A close-up photograph.
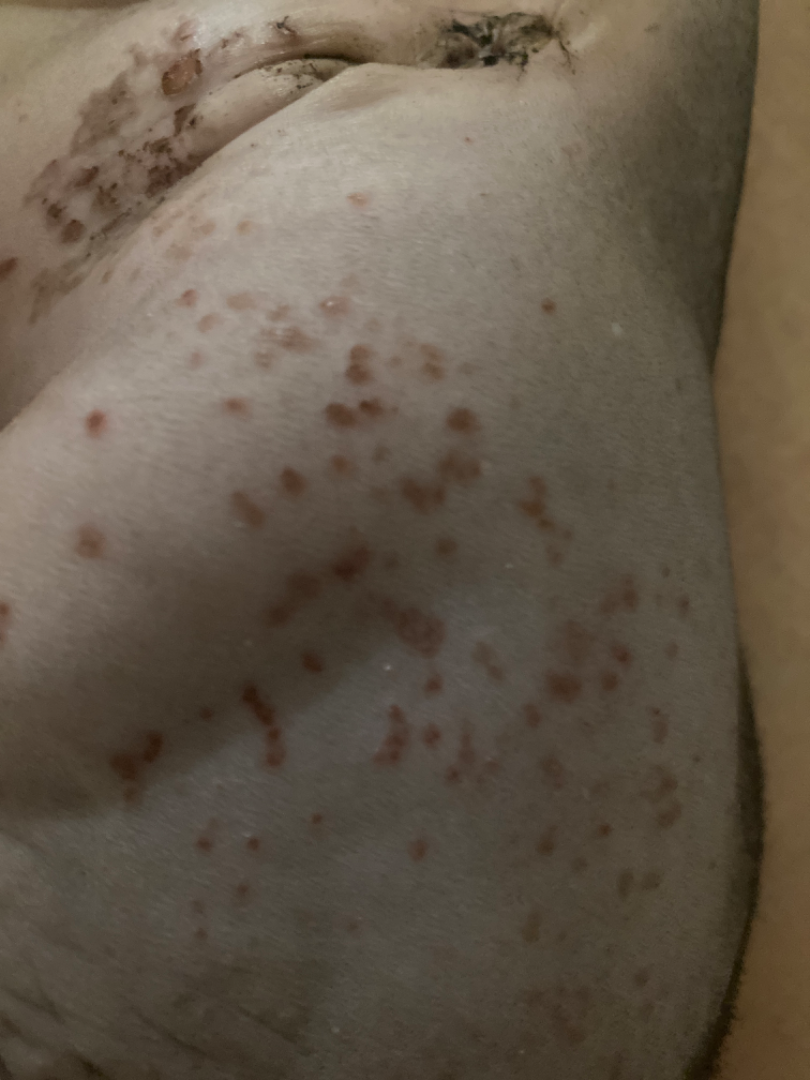| field | value |
|---|---|
| assessment | ungradable on photographic review |